Skin tone: Fitzpatrick I; close-up view:
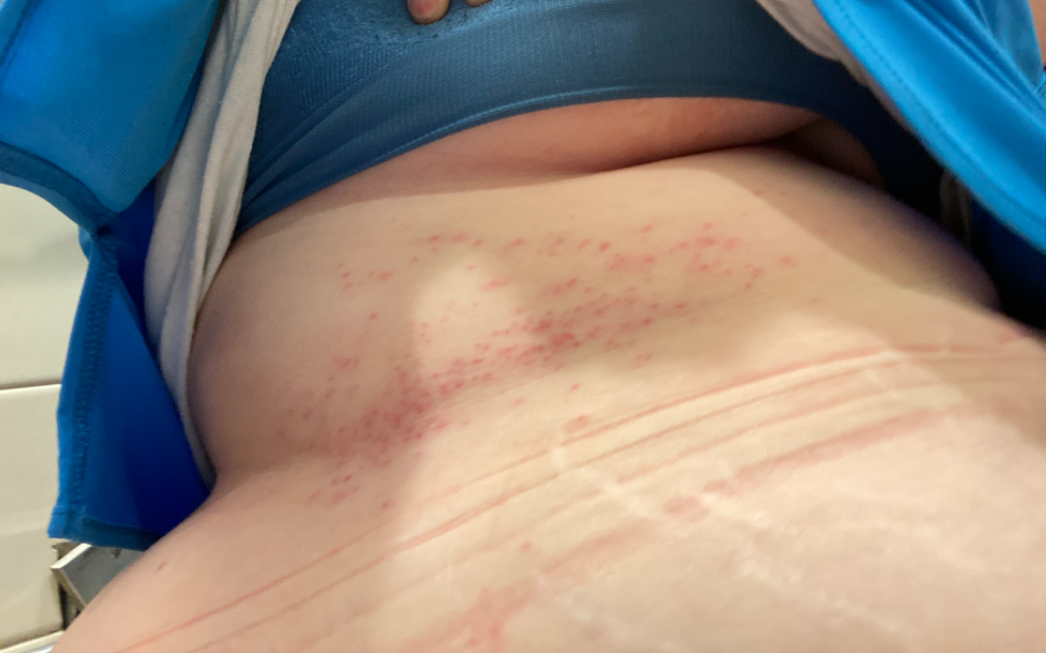impression = the differential is split between Intertrigo and Herpes Zoster; a remote consideration is Irritant Contact Dermatitis.